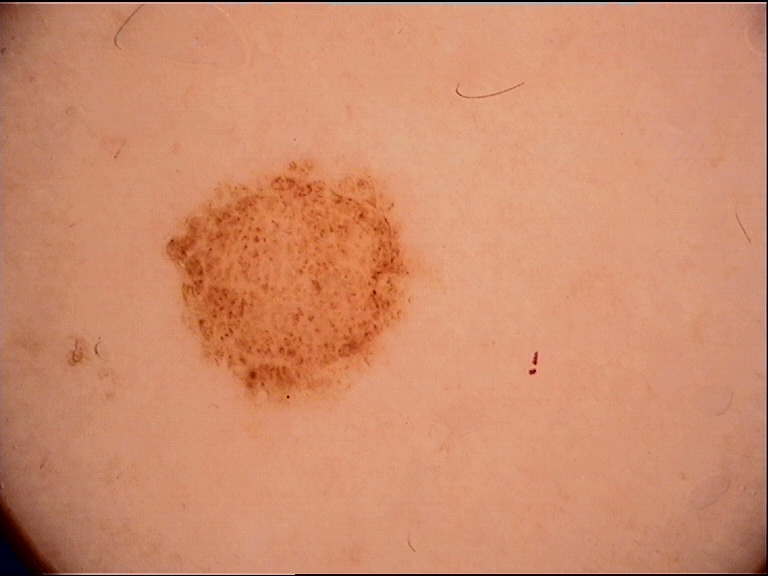Summary:
The architecture is that of a banal lesion.
Conclusion:
The diagnostic label was a compound nevus.